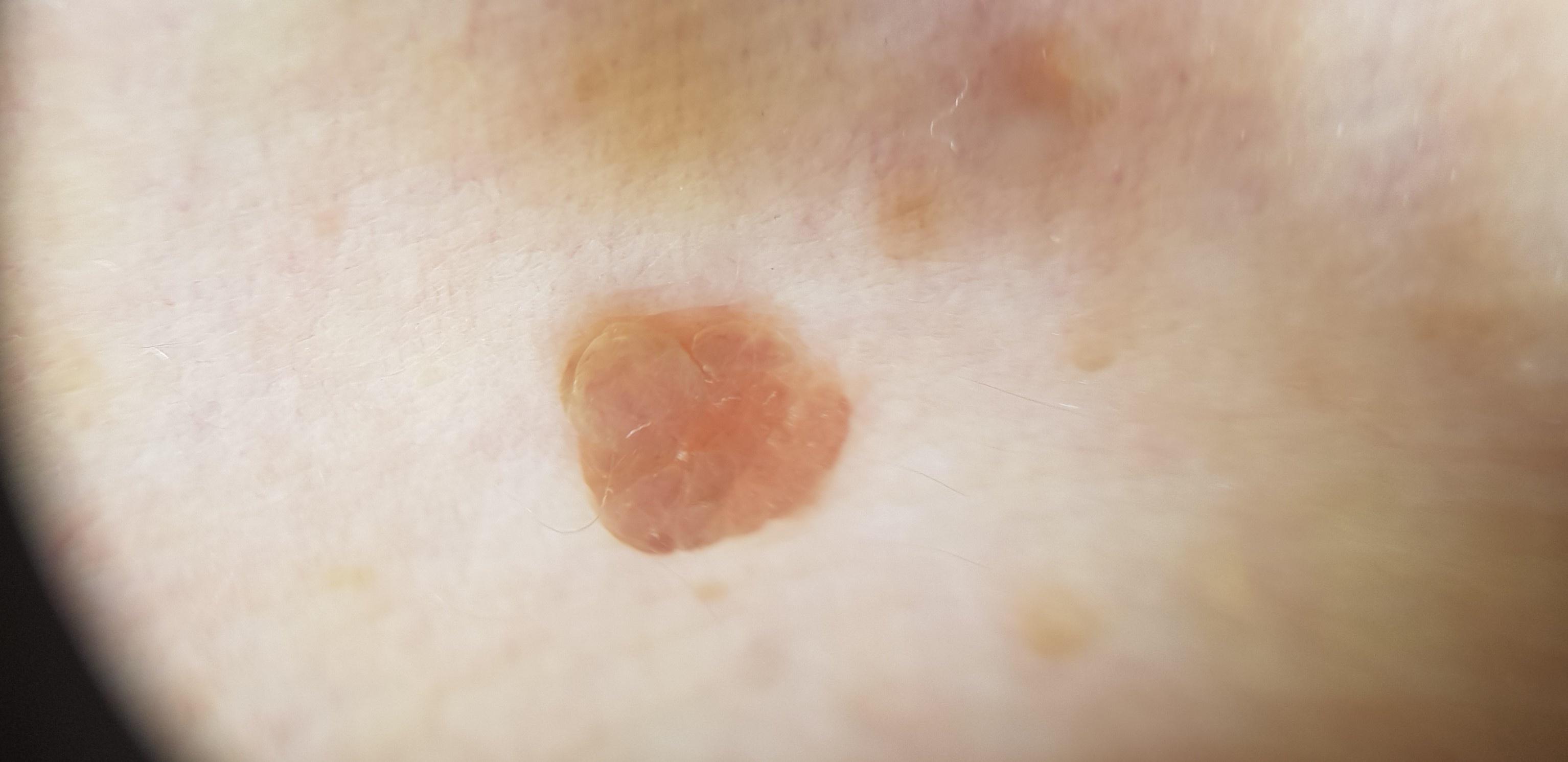A dermoscopic image of a skin lesion. A female subject aged 48 to 52. The patient was assessed as Fitzpatrick phototype III. The lesion is located on the trunk. Histopathological examination showed a benign lesion — a nevus.